An image taken at an angle · the lesion involves the front of the torso · the subject is 18–29, male.
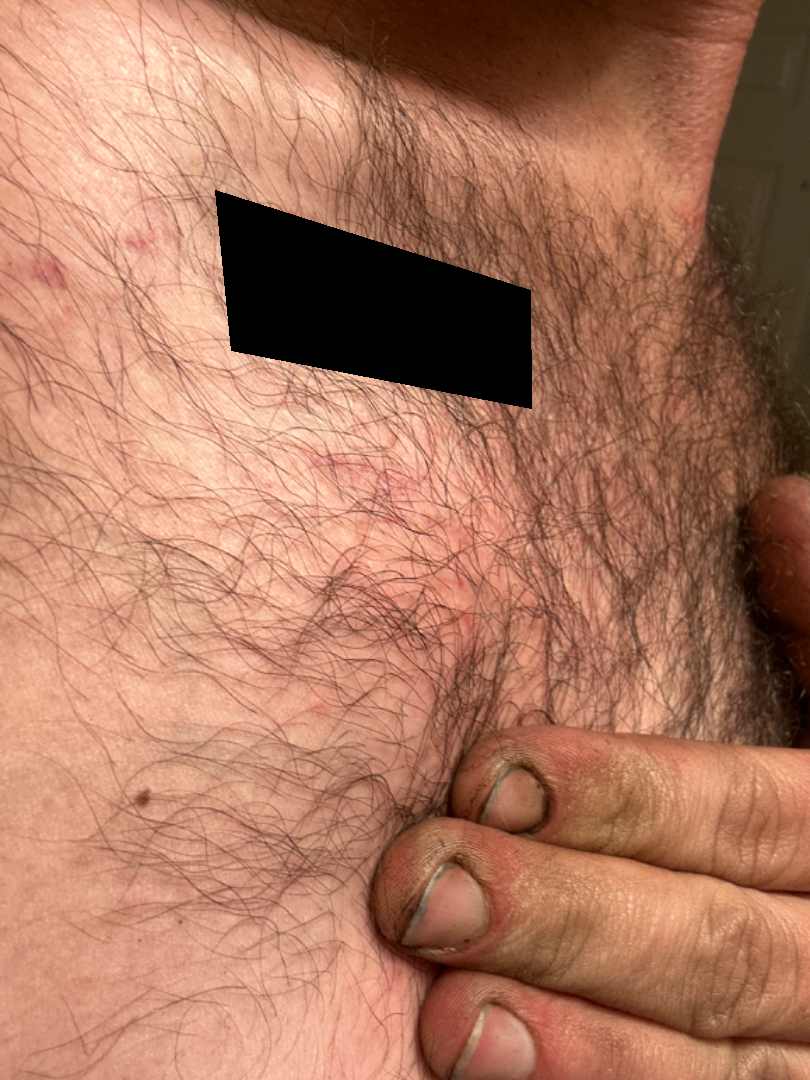Case summary:
- assessment — ungradable on photographic review
- reported symptoms — none reported
- lesion texture — flat
- present for — about one day
- patient describes the issue as — acne